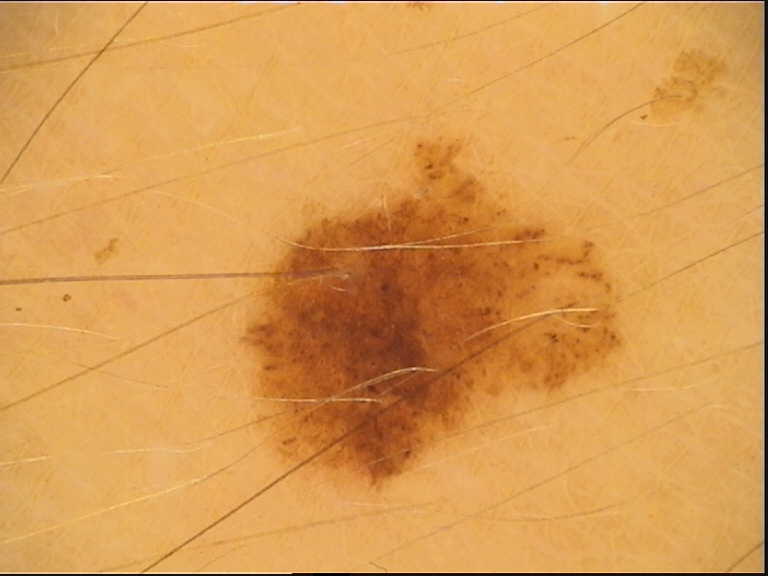Dermoscopy of a skin lesion. Classified as a dysplastic compound nevus.